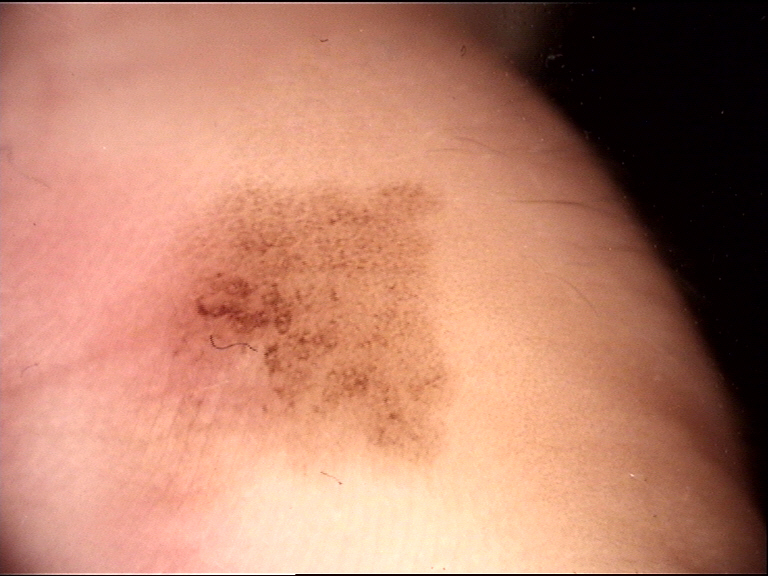Case:
- class — acral junctional nevus (expert consensus)